The patient says their skin reddens painfully with sun exposure; a female patient age 81; a dermatoscopic image of a skin lesion; collected as part of a research study, without a referral diagnosis.
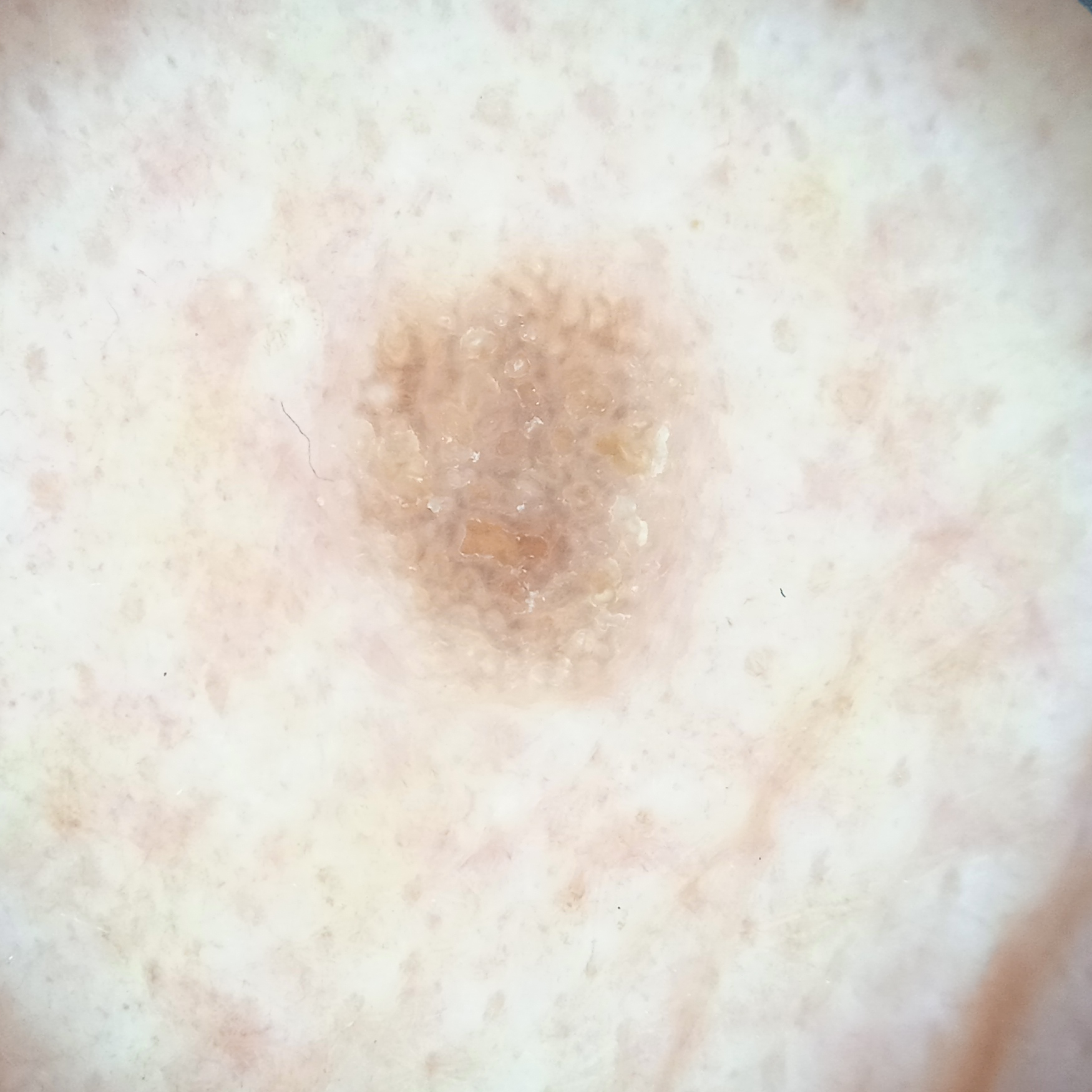lesion size: 5.3 mm | assessment: seborrheic keratosis (dermatologist consensus).